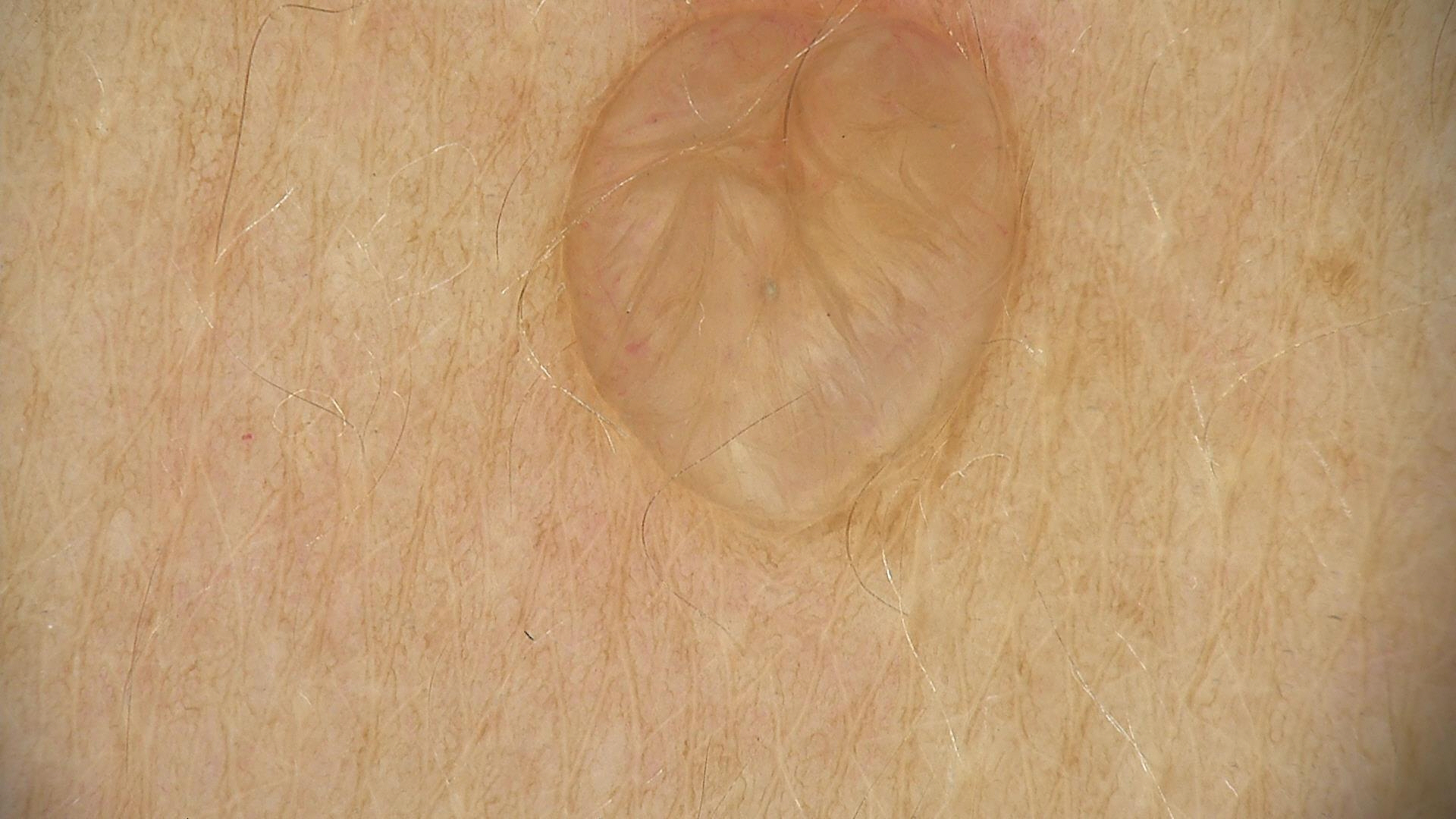The diagnosis was a banal lesion — a dermal nevus.